The photo was captured at an angle; the lesion involves the arm and front of the torso; female contributor, age 40–49 — 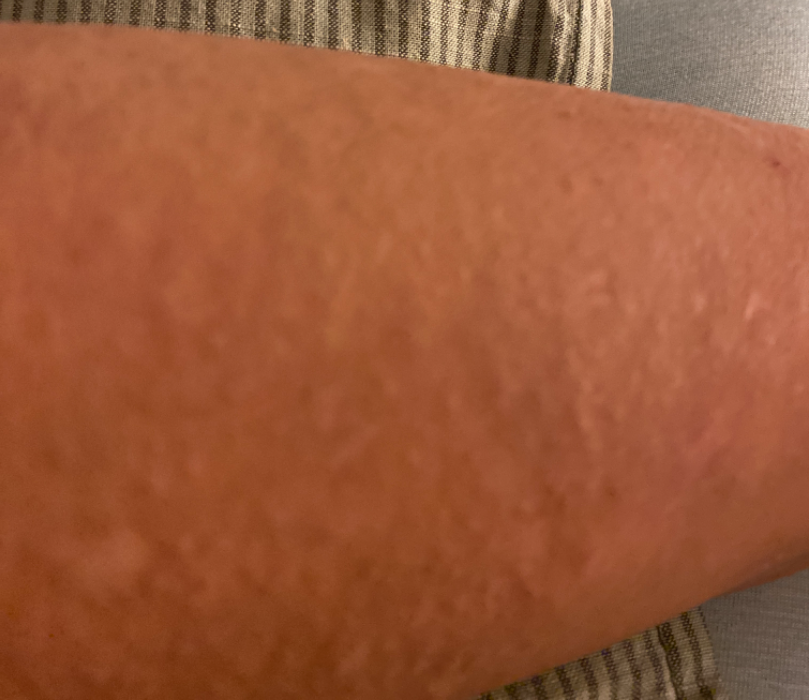| feature | finding |
|---|---|
| differential | most consistent with Folliculitis |